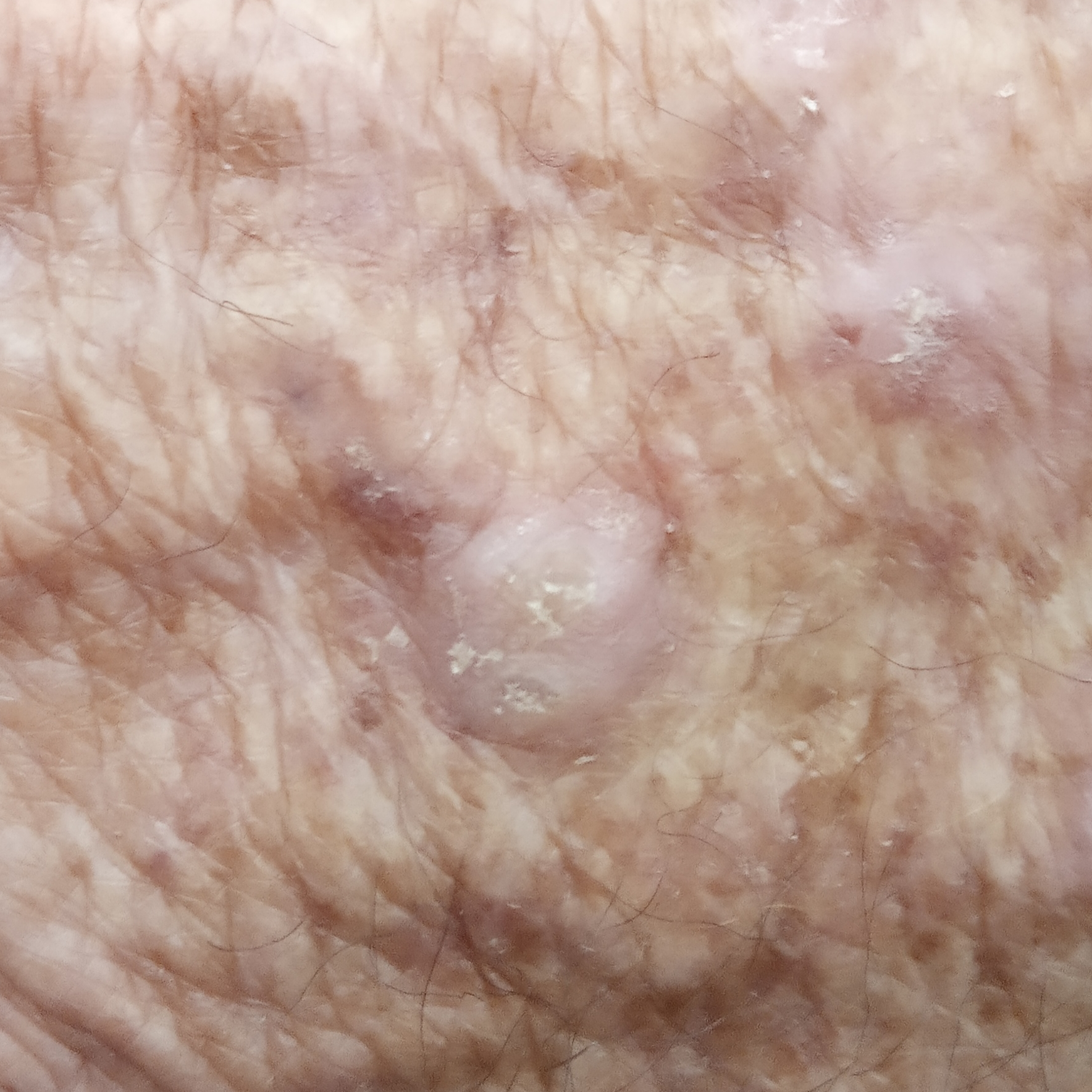Q: Tell me about the patient.
A: male, age 69
Q: Any reported symptoms?
A: elevation, change in appearance, itching, growth / no pain, no bleeding
Q: What did the workup show?
A: squamous cell carcinoma (biopsy-proven)